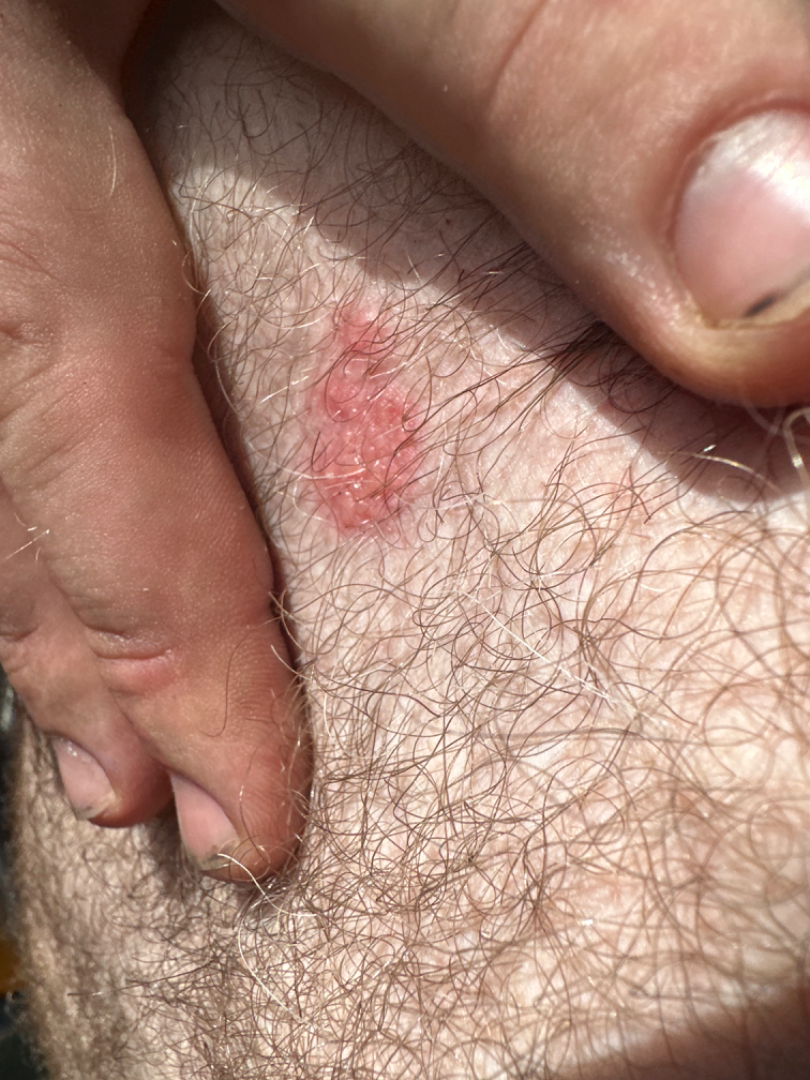Q: What is the affected area?
A: back of the torso and front of the torso
Q: What is the framing?
A: at an angle
Q: What is the dermatologist's impression?
A: a single dermatologist reviewed the case: favoring Condyloma acuminatum; also consider Melanocytic Nevus